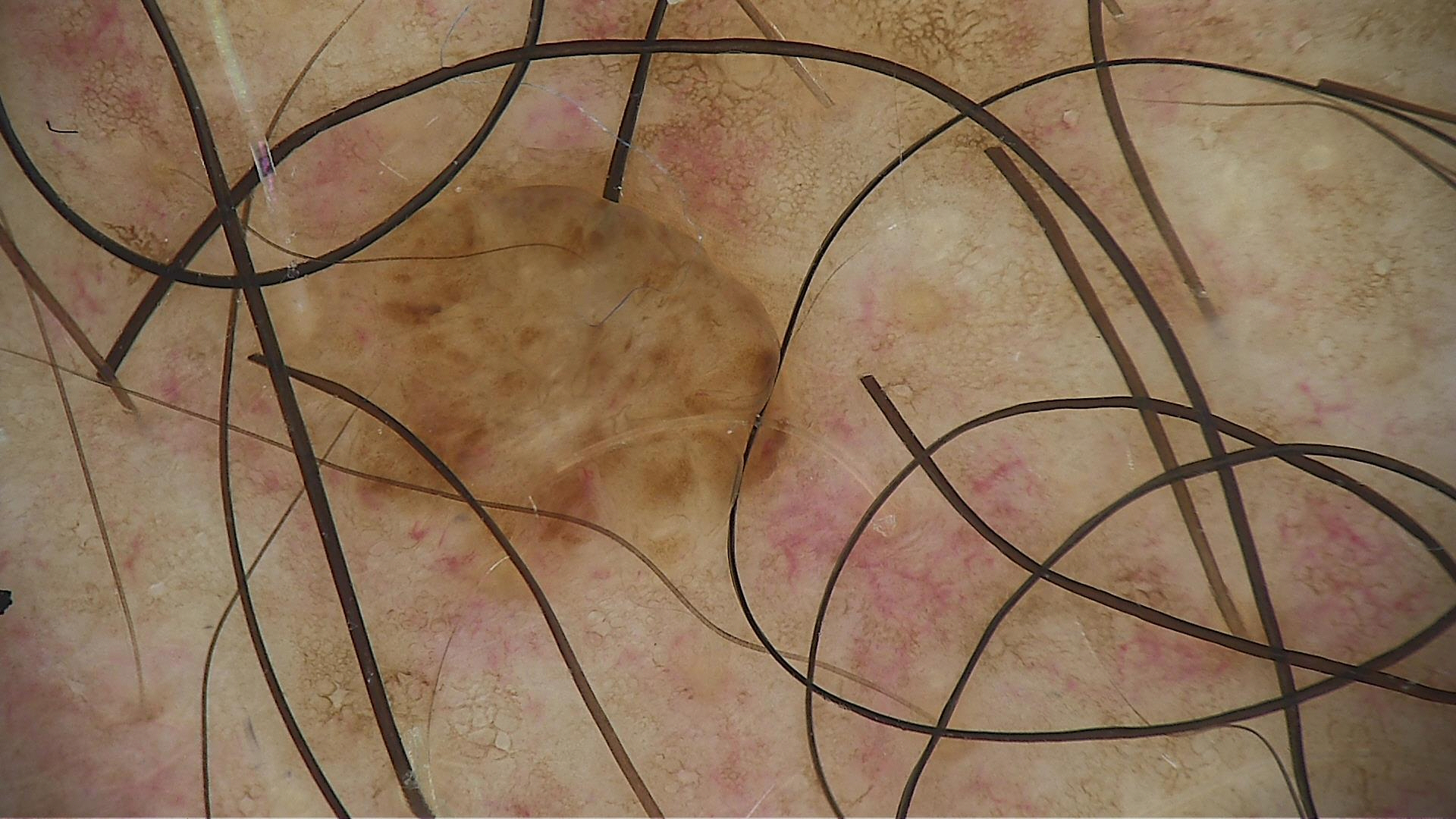The diagnostic label was a compound nevus.